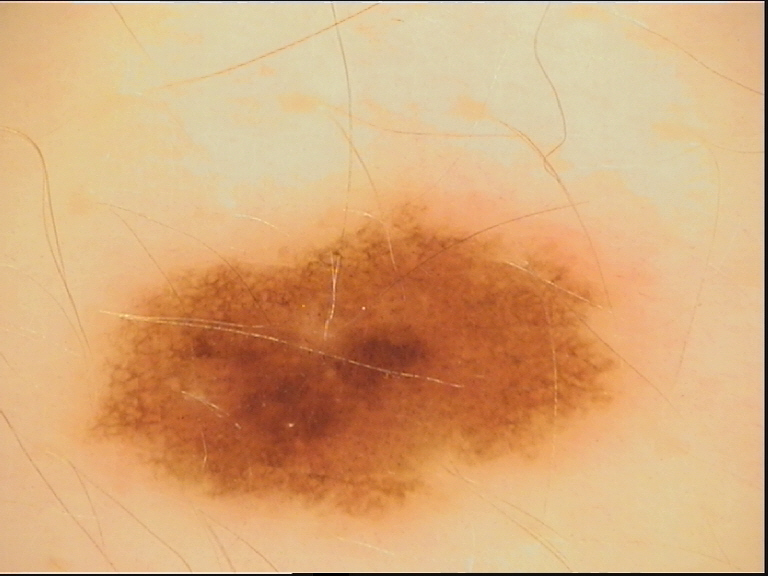The diagnosis was a dysplastic junctional nevus.